A close-up photograph. Female subject, age 60–69. The lesion involves the leg — 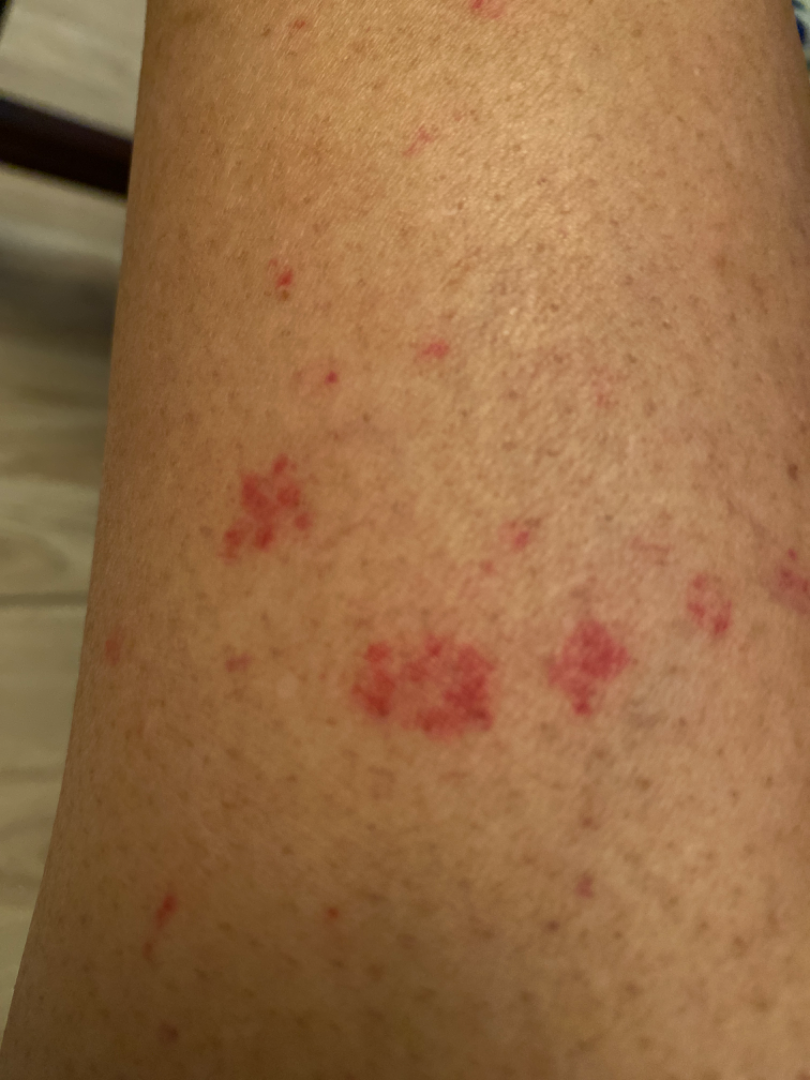Reviewed remotely by one dermatologist: the impression was split between Purpura and Leukocytoclastic Vasculitis.